A female patient approximately 80 years of age; a contact-polarized dermoscopy image of a skin lesion — 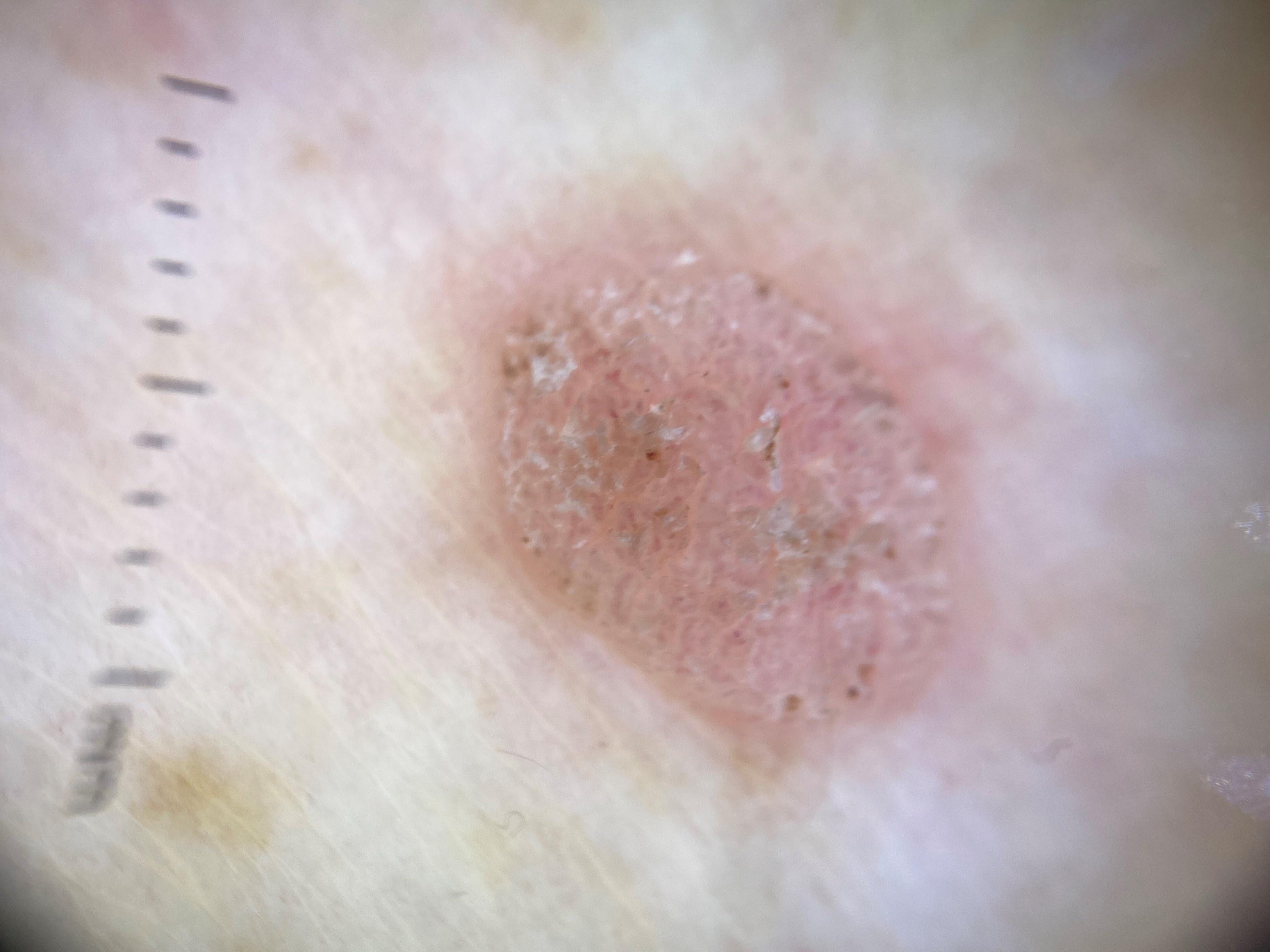site = a lower extremity
diagnosis = Seborrheic keratosis (biopsy-proven)